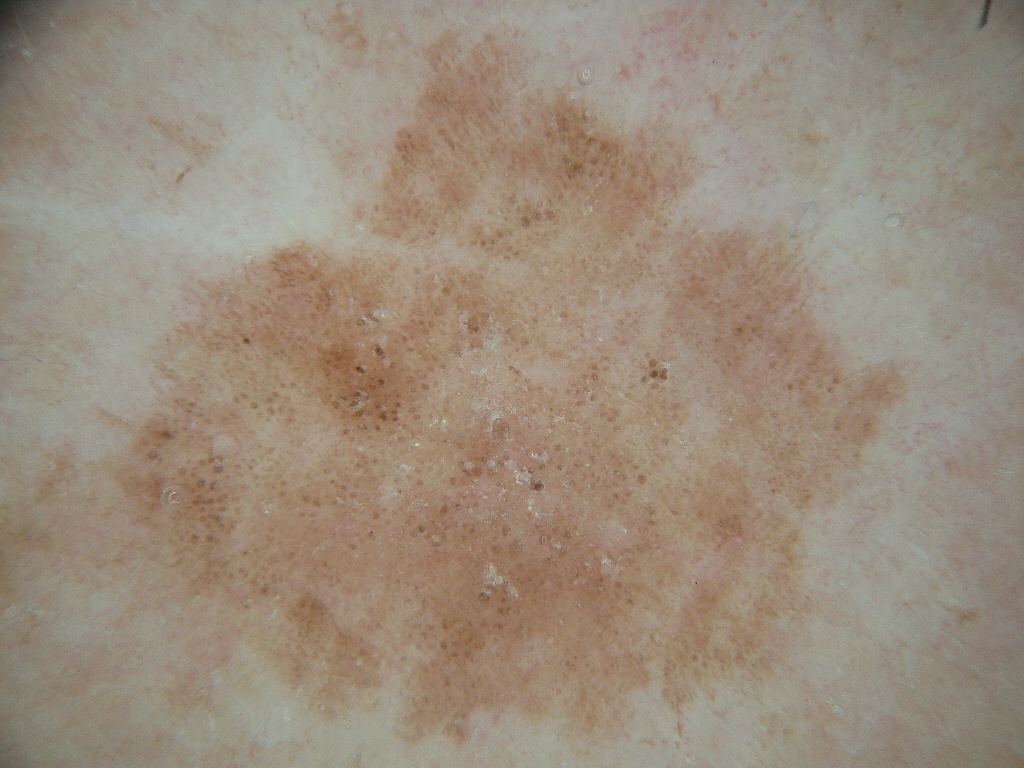Summary:
A dermatoscopic image of a skin lesion. In (x1, y1, x2, y2) order, the visible lesion spans <box>90, 9, 914, 766</box>.
Conclusion:
The lesion was assessed as a benign lesion.